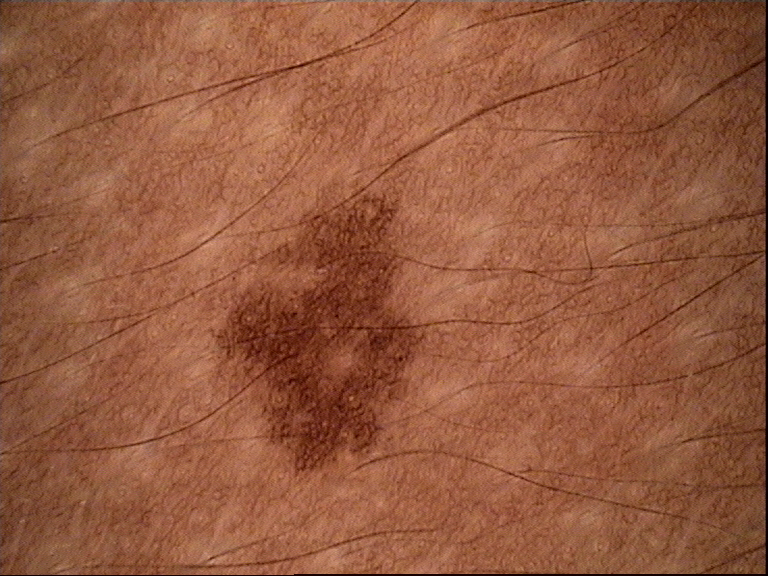The diagnostic label was a dysplastic junctional nevus.